The photo was captured at a distance; the head or neck is involved; the subject is a female aged 18–29: 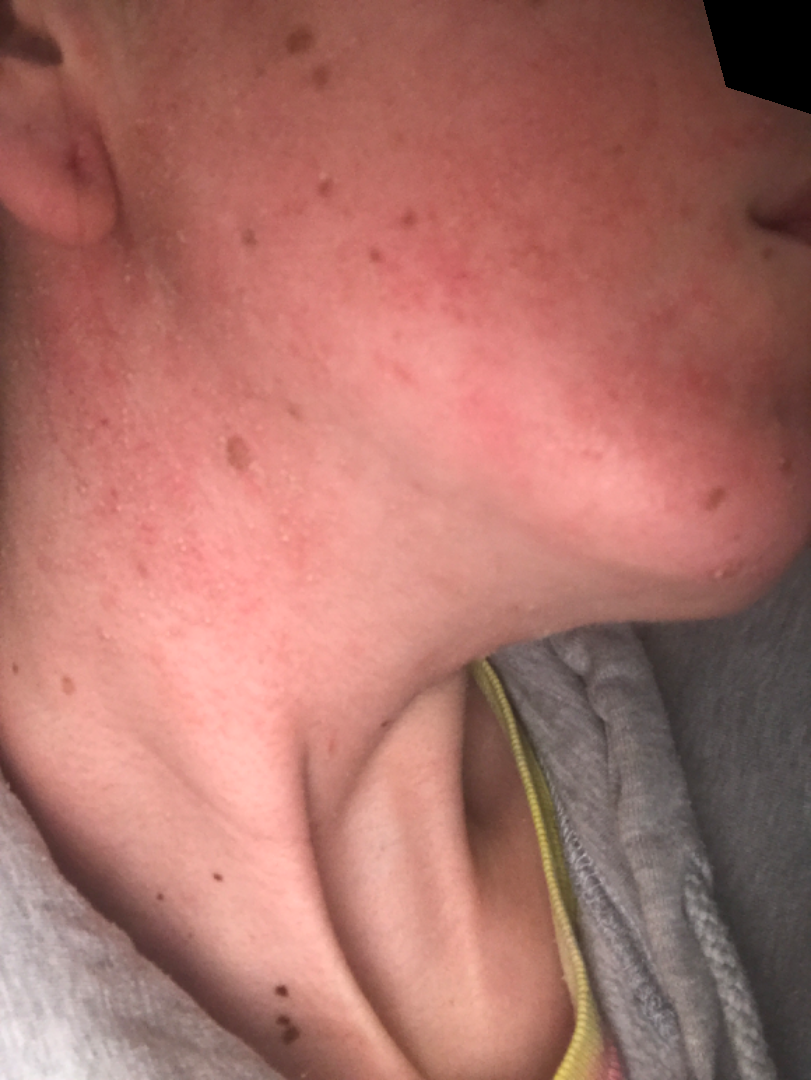Q: What was the assessment?
A: indeterminate
Q: When did this start?
A: less than one week
Q: Patient's own categorization?
A: a rash
Q: Constitutional symptoms?
A: fever and mouth sores
Q: What is the lesion texture?
A: fluid-filled and rough or flaky